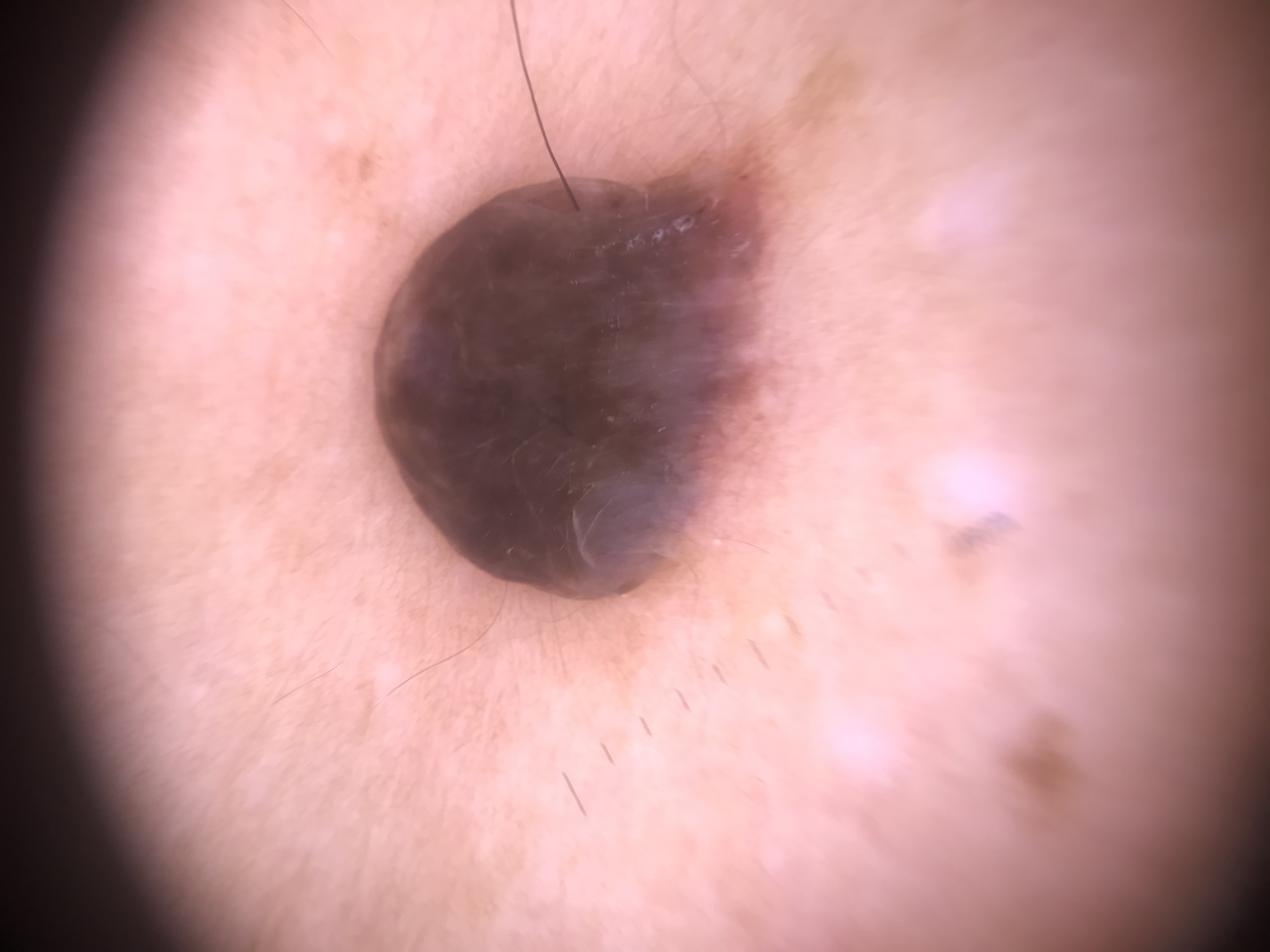Impression:
Classified as a dermal nevus.